The affected area is the top or side of the foot; female subject, age 18–29; self-categorized by the patient as a rash; this image was taken at an angle; the condition has been present for about one day; symptoms reported: itching; no associated systemic symptoms reported; the lesion is described as raised or bumpy:
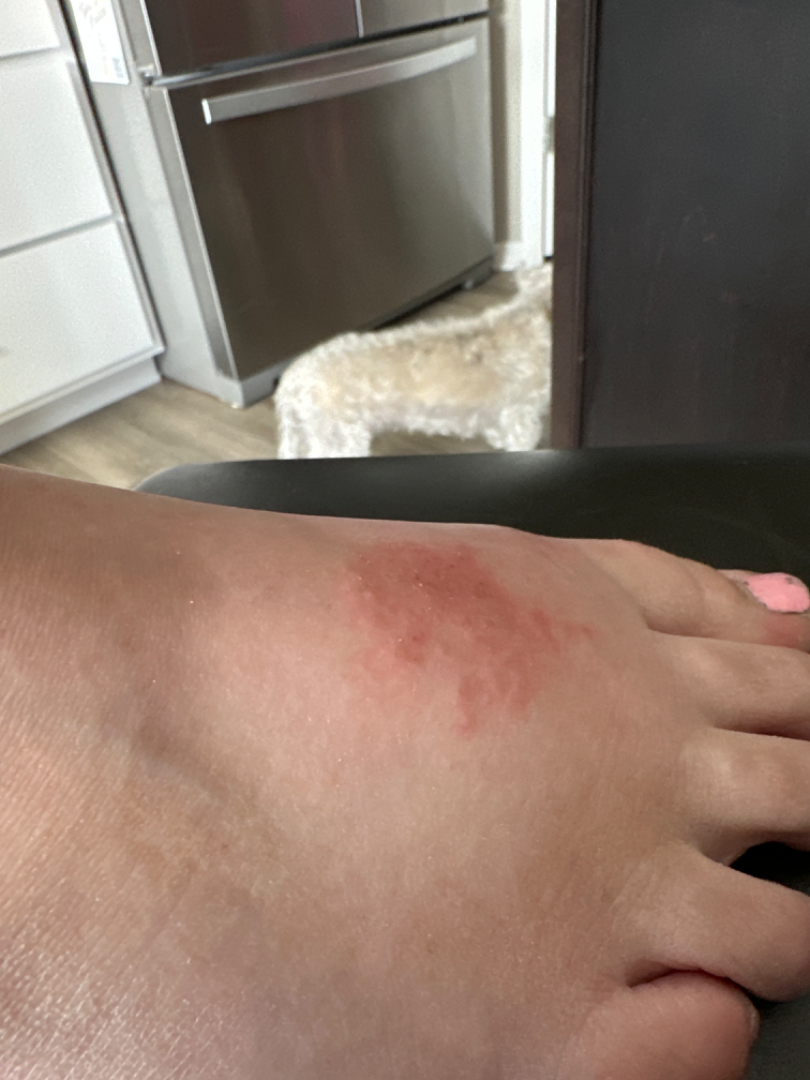Review:
One reviewing dermatologist: most likely Allergic Contact Dermatitis; the differential also includes Eczema.